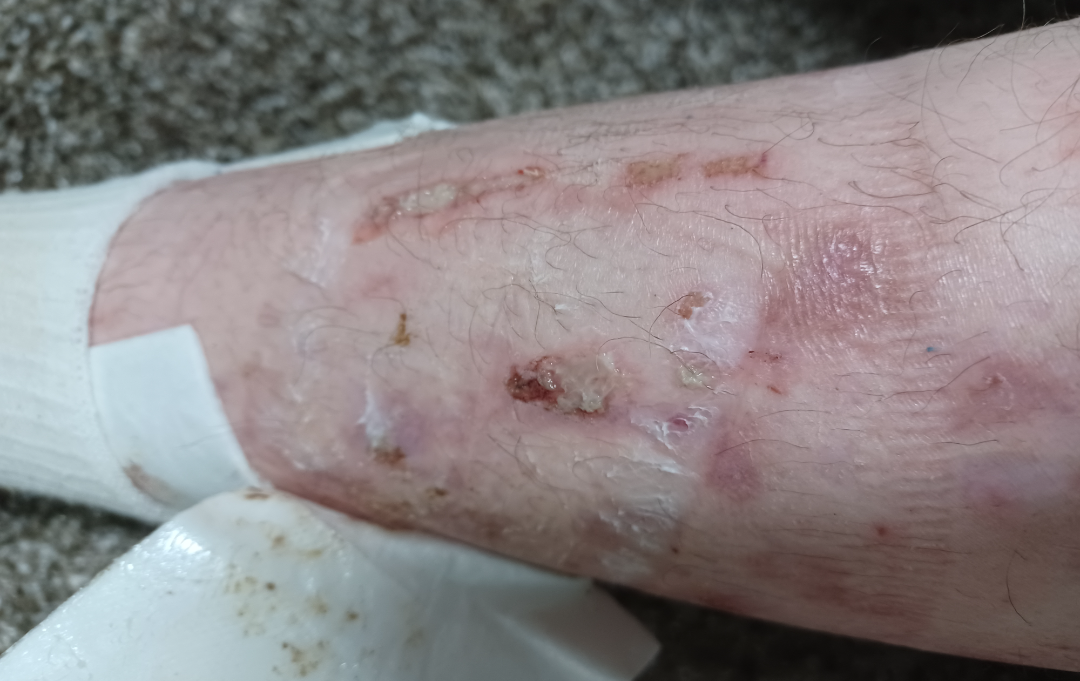Findings: No differential diagnosis could be assigned on photographic review.